Dermoscopy of a skin lesion:
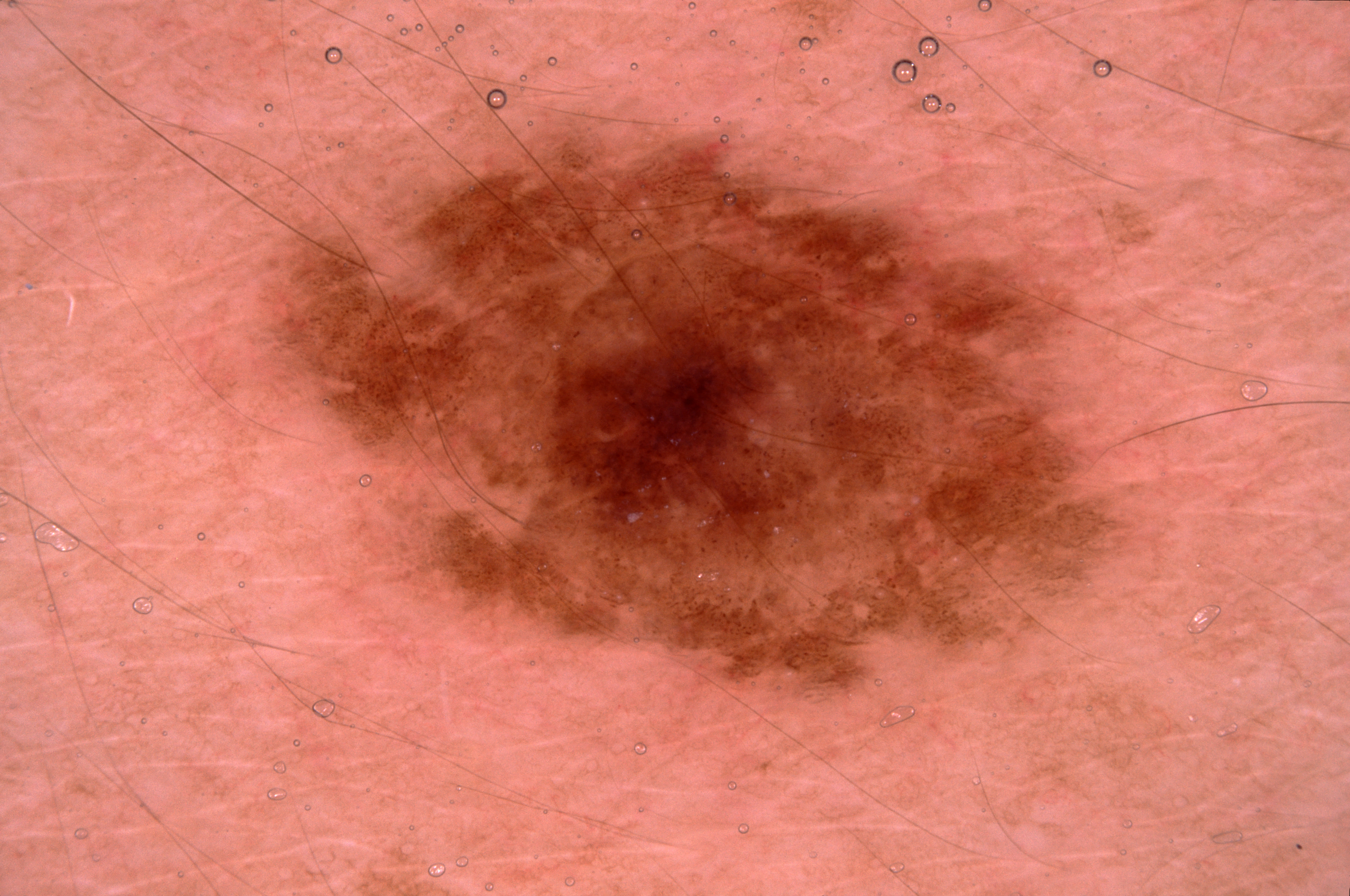• bounding box: bbox=[274, 133, 1118, 693]
• features: milia-like cysts
• diagnosis: a melanocytic nevus